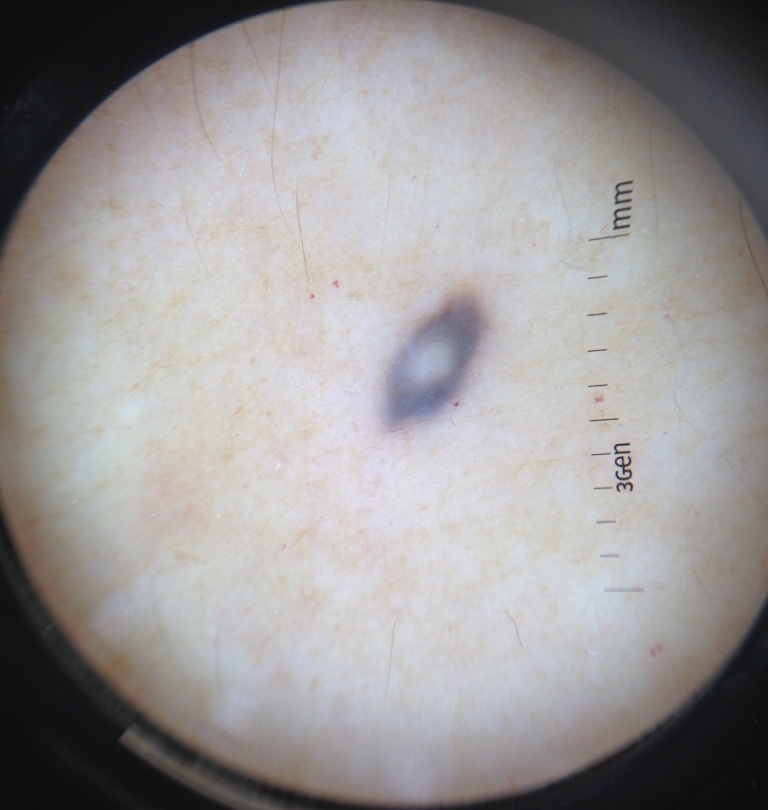A skin lesion imaged with a dermatoscope. Consistent with a dermal lesion — a blue nevus.